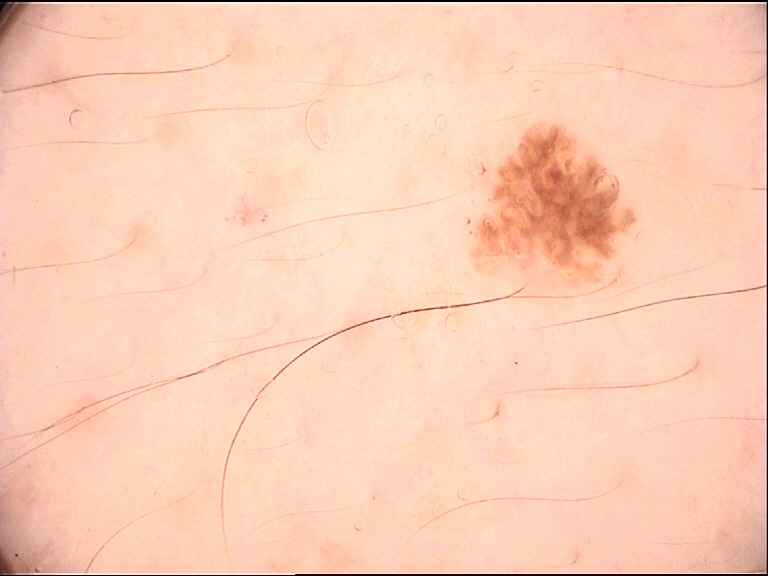Case:
* diagnosis — dysplastic junctional nevus (expert consensus)